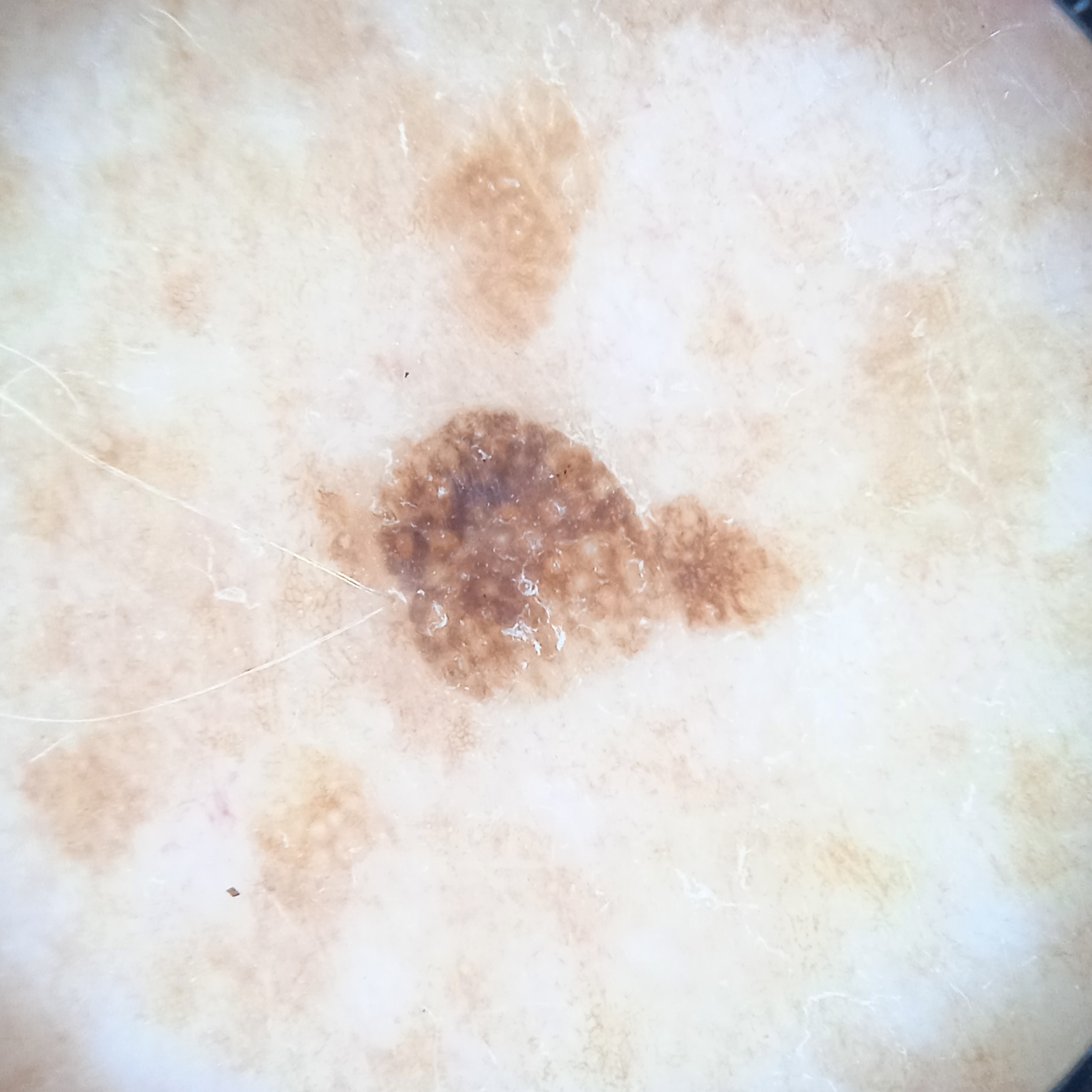By self-report, a personal history of cancer. A dermoscopic image of a skin lesion. The patient says their skin reddens with sun exposure. The patient describes having numerous moles. A male patient aged 73. The lesion is located on the back. The lesion is about 5.5 mm across. The consensus diagnosis for this lesion was a seborrheic keratosis.